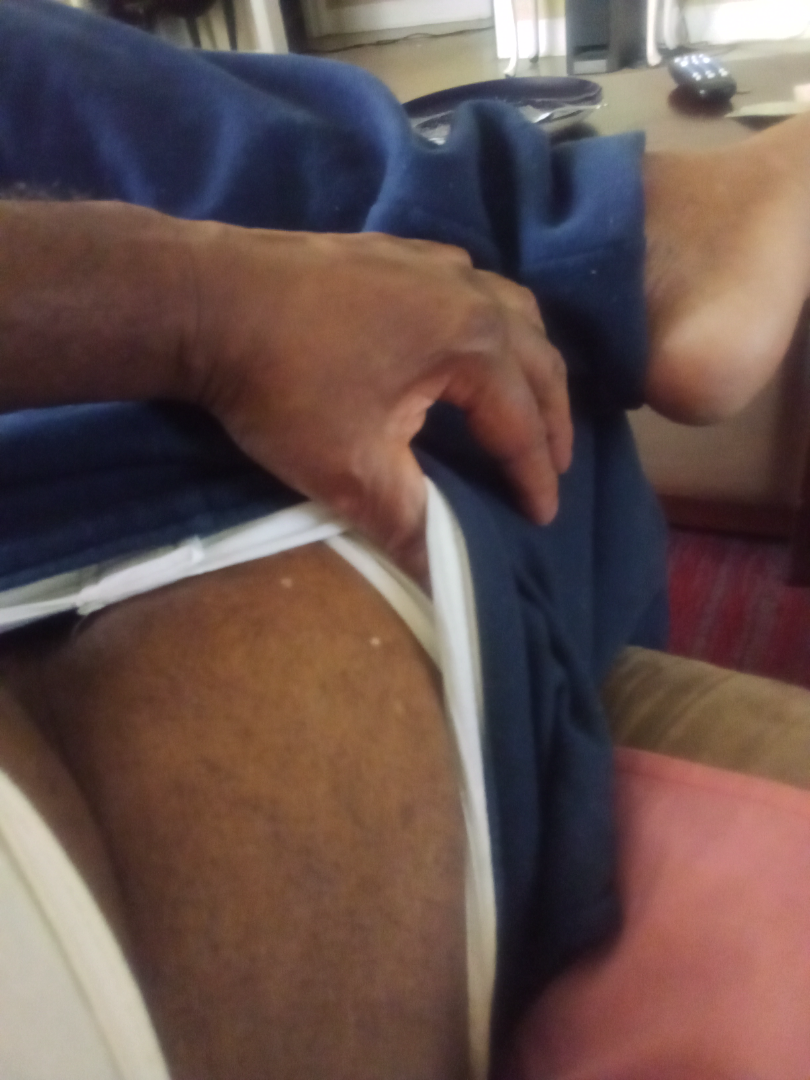assessment: unable to determine | surface texture: flat | patient-reported symptoms: bothersome appearance | anatomic site: arm | shot type: at a distance | self-categorized as: hair loss | onset: one to three months | skin tone: FST V.